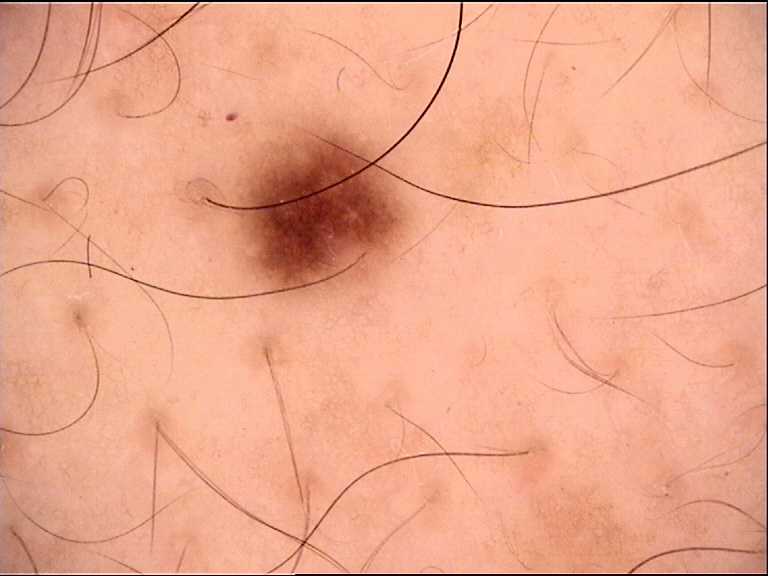Conclusion:
Labeled as a junctional nevus.